A dermatoscopic image of a skin lesion:
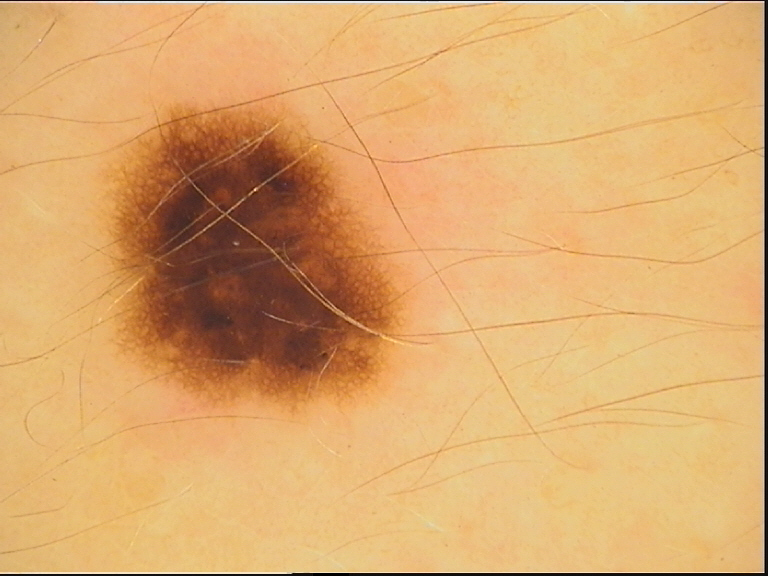Labeled as a dysplastic junctional nevus.